A dermoscopy image of a single skin lesion.
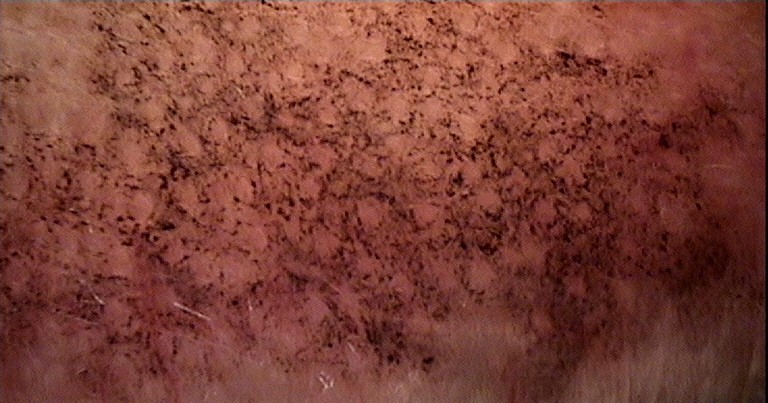class: ink-spot lentigo (expert consensus).